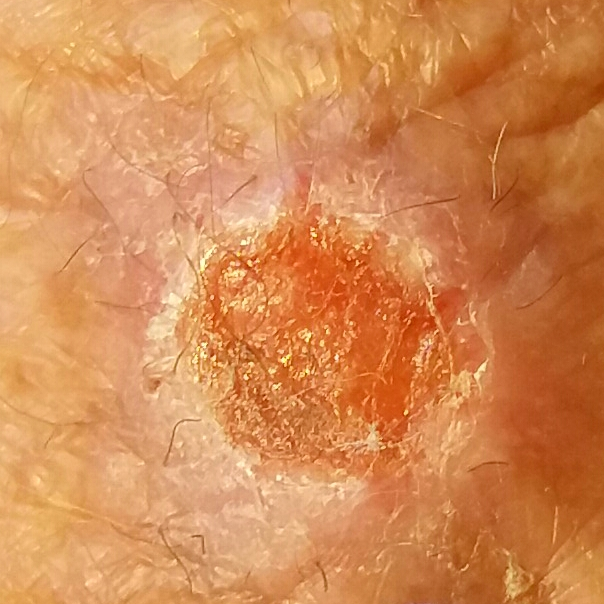image type=clinical photo
patient=female, age 75
site=a forearm
patient-reported symptoms=bleeding, elevation, growth / no itching
pathology=basal cell carcinoma (biopsy-proven)